A dermoscopic close-up of a skin lesion: 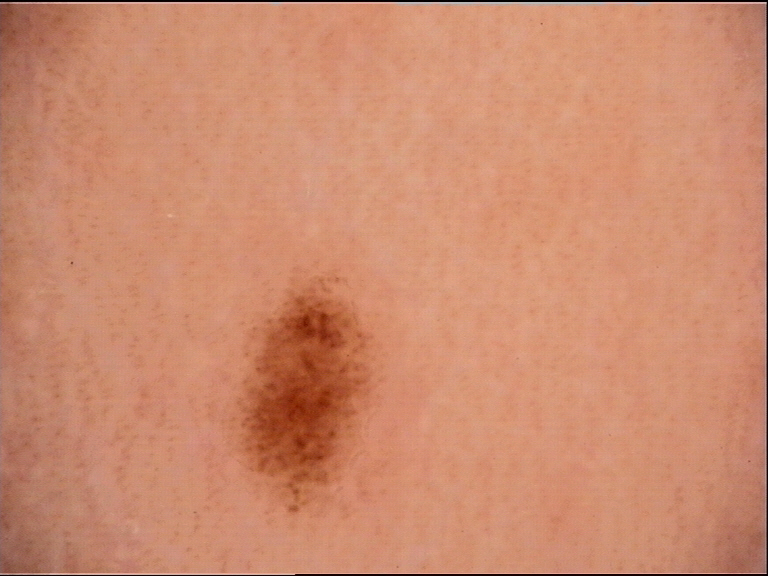The architecture is that of a banal lesion. Diagnosed as a junctional nevus.